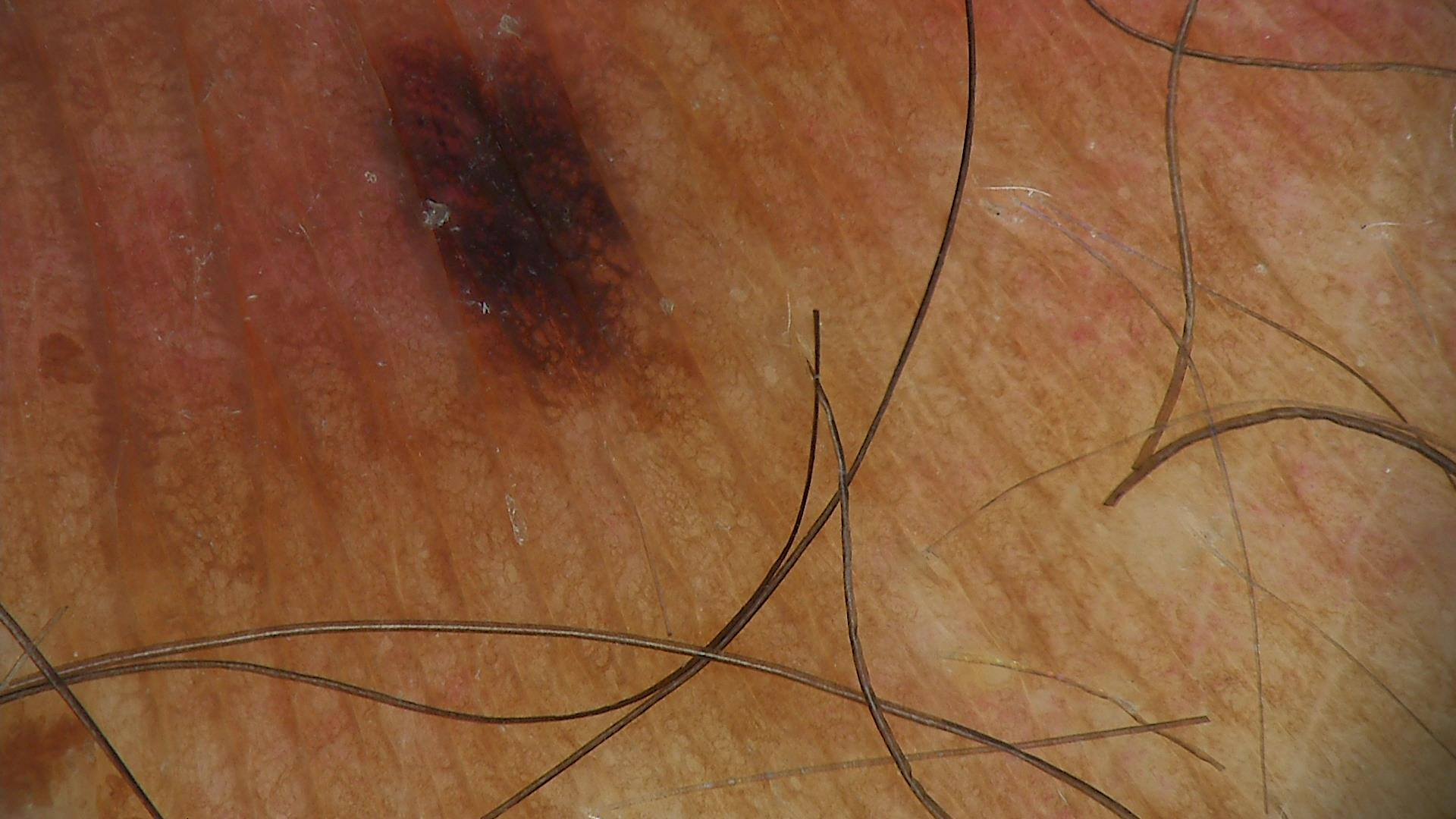A skin lesion imaged with a dermatoscope. Labeled as an acral dysplastic junctional nevus.